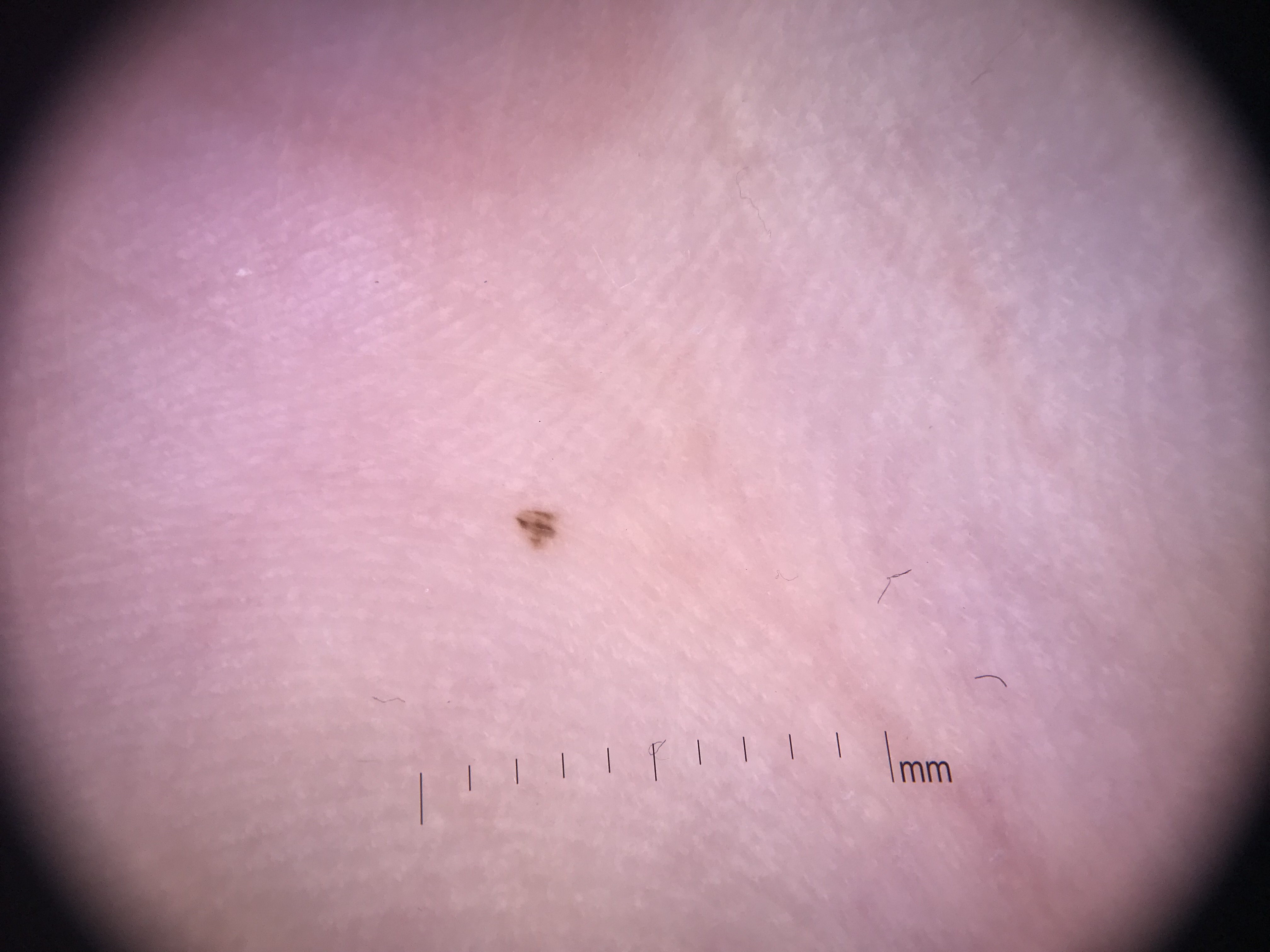Dermoscopy of a skin lesion.
Diagnosed as a banal lesion — an acral junctional nevus.